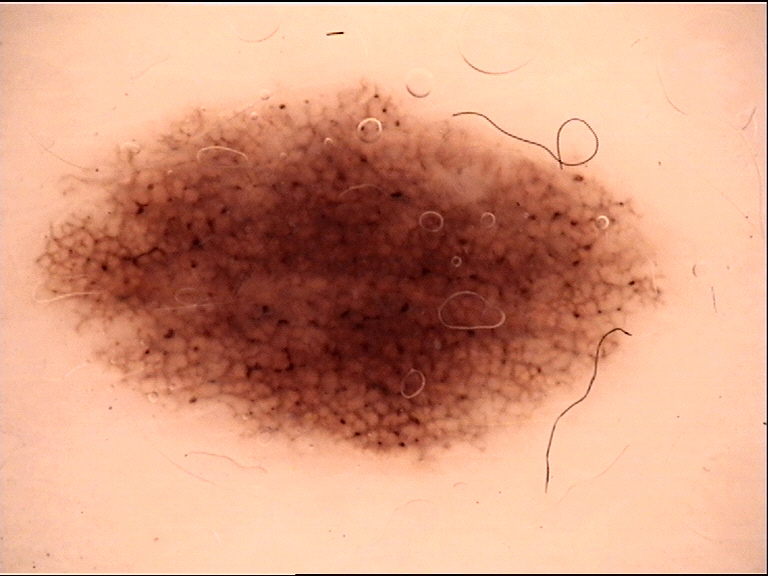Summary:
A dermatoscopic image of a skin lesion.
Impression:
The diagnosis was a benign lesion — a dysplastic junctional nevus.